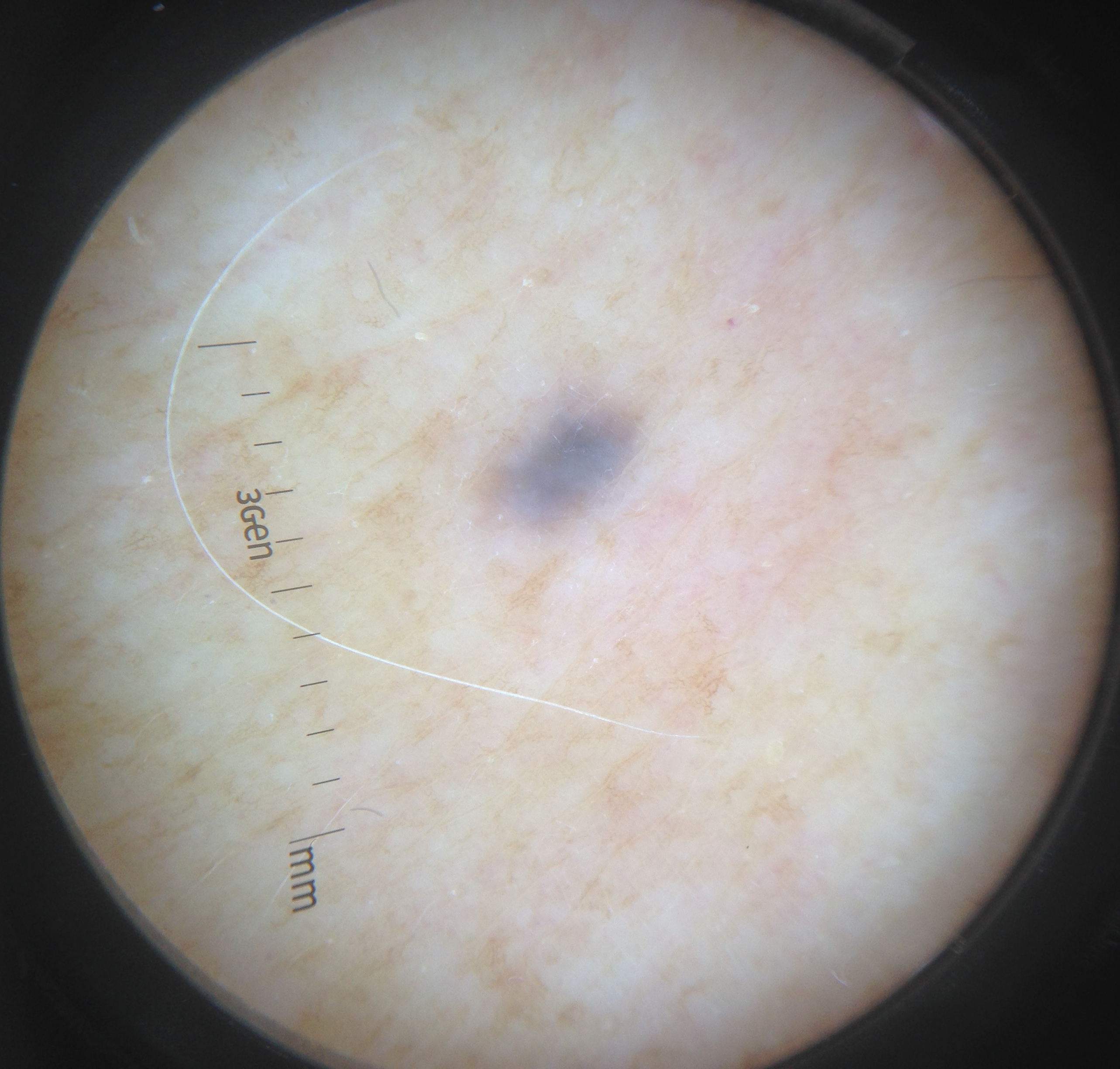| feature | finding |
|---|---|
| diagnosis | blue nevus (expert consensus) |